A female subject aged 66:
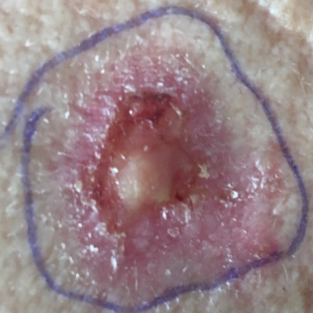Case:
– location — the back
– symptoms — bleeding, itching, pain, elevation / no growth
– diagnosis — basal cell carcinoma (biopsy-proven)